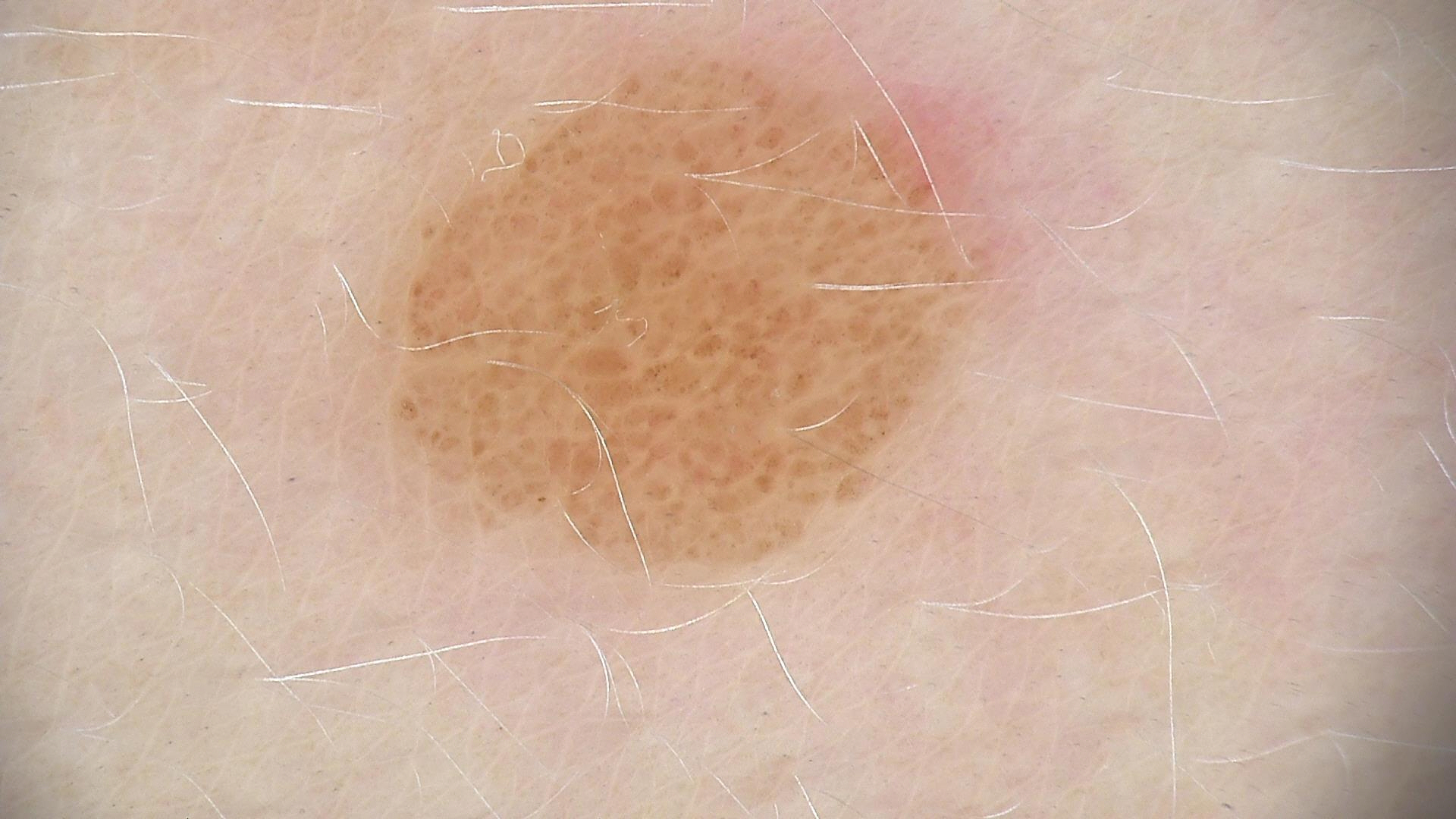A dermoscopy image of a single skin lesion. Diagnosed as a banal lesion — a compound nevus.